Dermoscopy of a skin lesion:
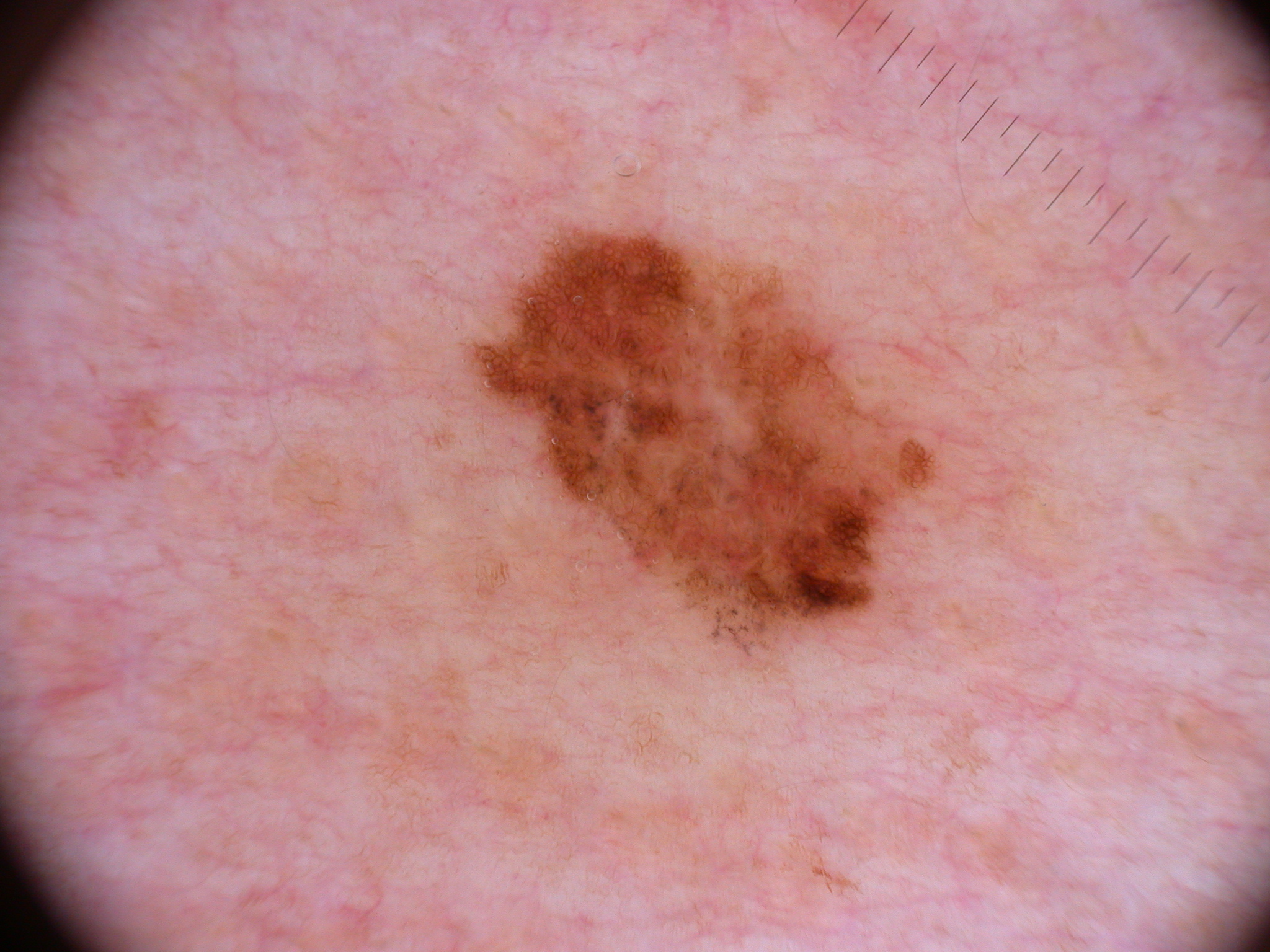features = pigment network; absent: negative network, globules, milia-like cysts, and streaks
bounding box = x1=467, y1=229, x2=939, y2=652
assessment = a melanoma, a malignant skin lesion